A male subject aged 83 or older · a dermatoscopic image of a skin lesion — 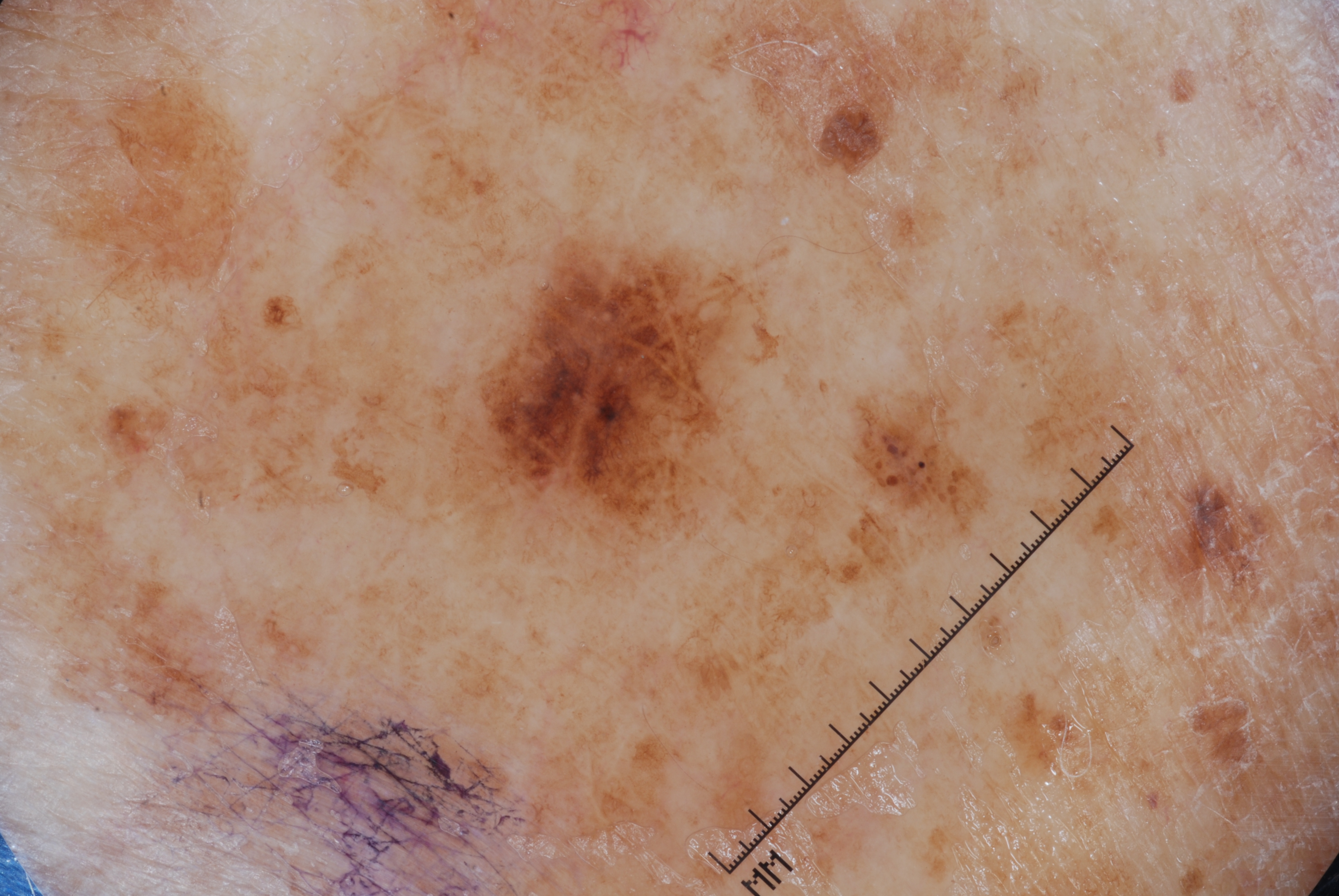The lesion's extent is x1=433, y1=209, x2=802, y2=623.
Dermoscopic examination shows pigment network and milia-like cysts.
The lesion takes up a moderate portion of the field.
Histopathology confirmed a melanoma, a malignant skin lesion.